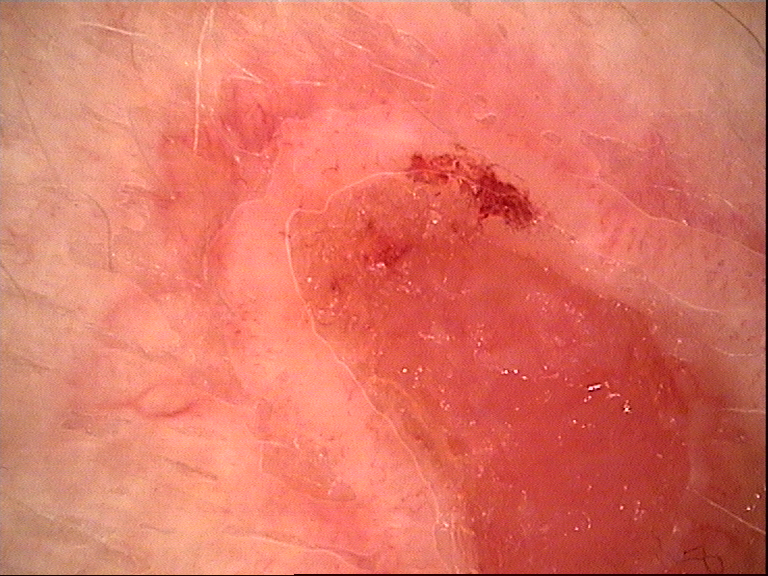  image: dermoscopy
  lesion_type:
    main_class: keratinocytic
  diagnosis:
    name: squamous cell carcinoma
    code: scc
    malignancy: malignant
    super_class: non-melanocytic
    confirmation: histopathology